A dermoscopic photograph of a skin lesion.
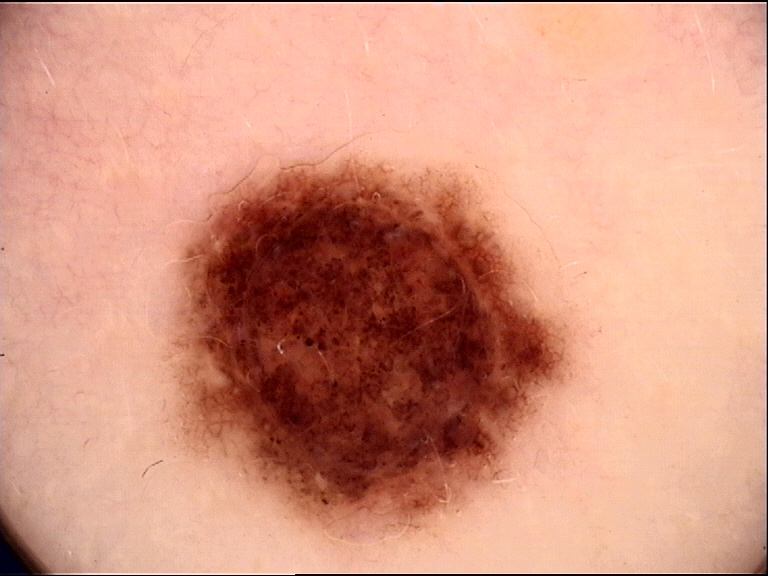assessment: dysplastic compound nevus (expert consensus)